Imaged for a research study, with no referral diagnosis recorded.
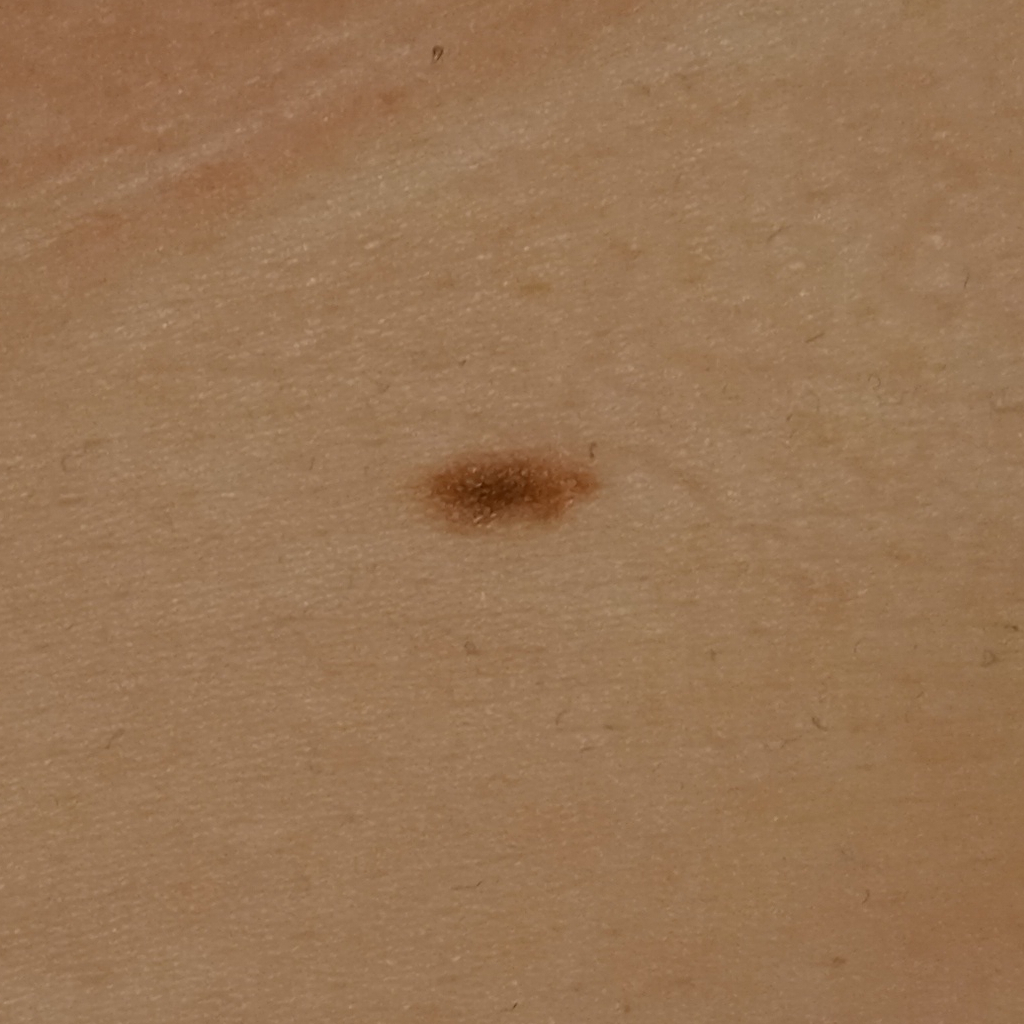anatomic site=the torso | lesion size=6.3 mm | assessment=melanocytic nevus (dermatologist consensus).